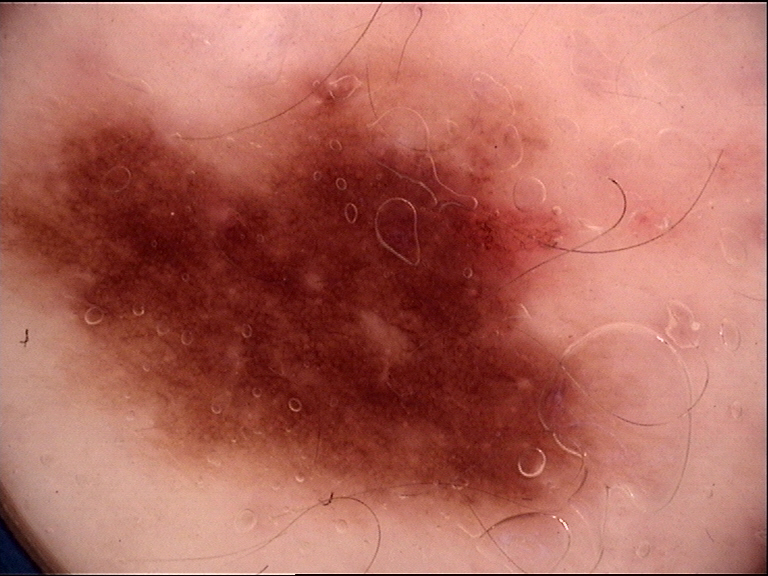modality: dermoscopy
label: dysplastic junctional nevus (expert consensus)